A dermoscopy image of a single skin lesion.
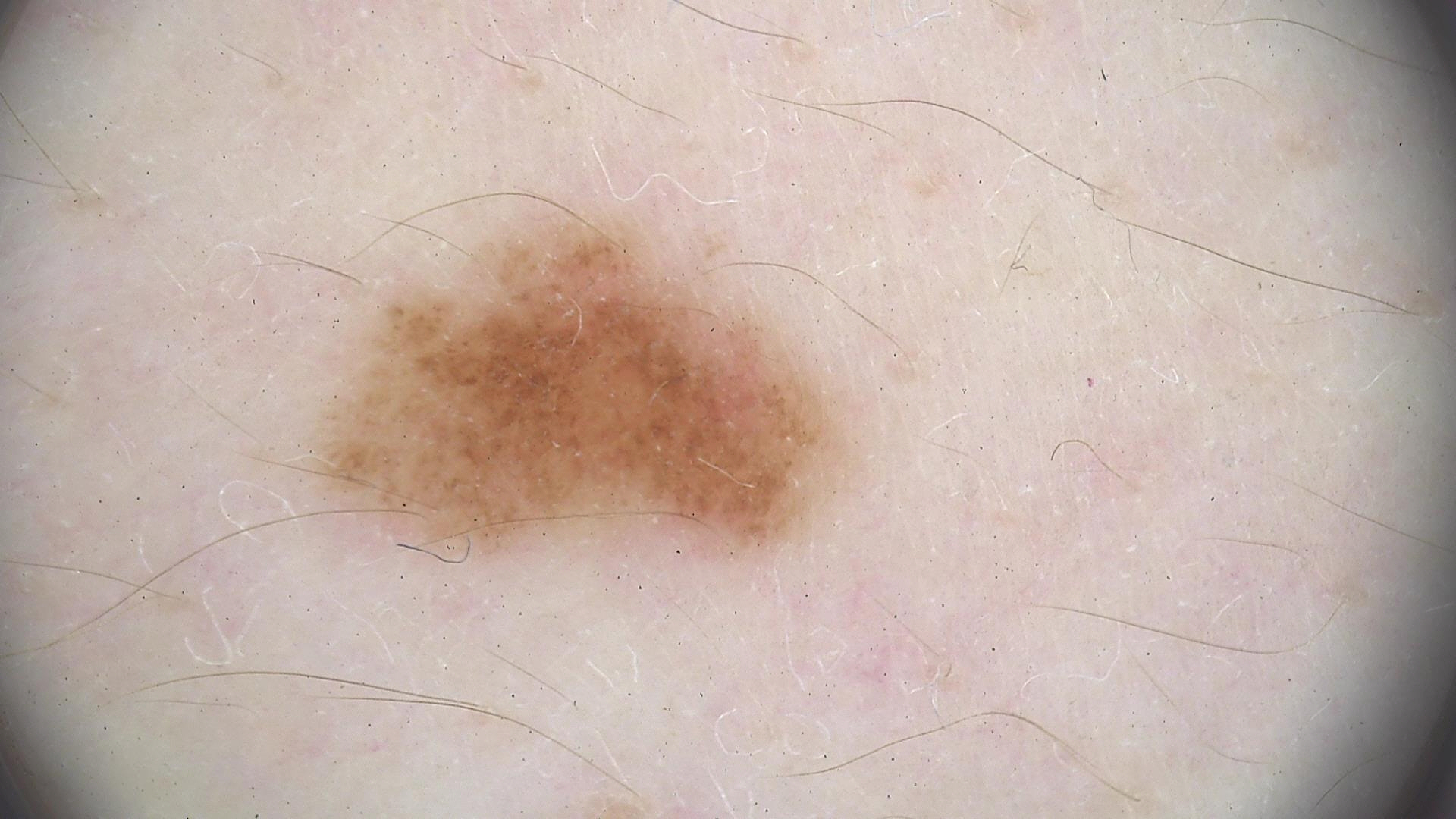Case:
– class · dysplastic junctional nevus (expert consensus)